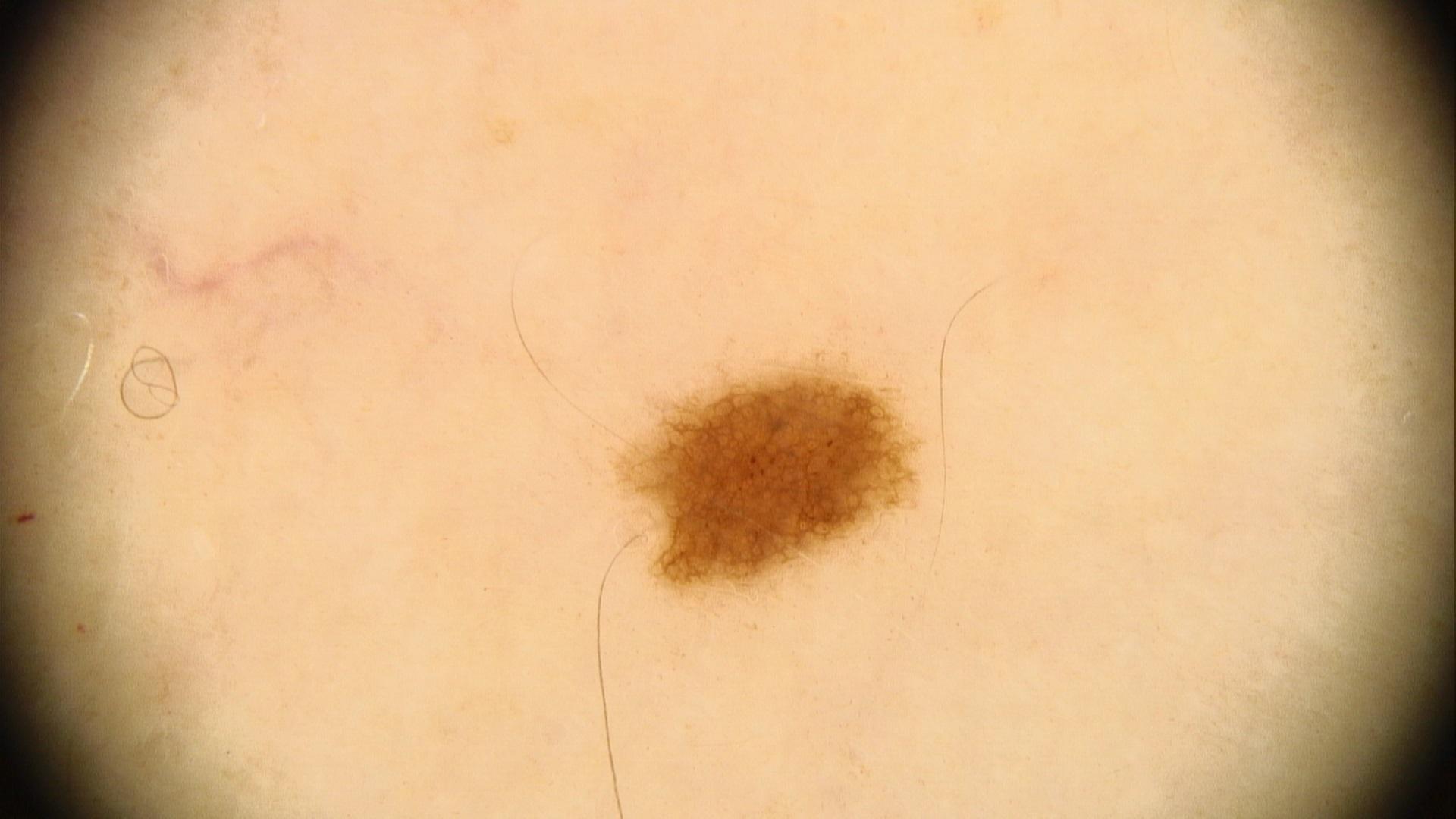diagnosis = Nevus (clinical impression).